A dermoscopic view of a skin lesion — 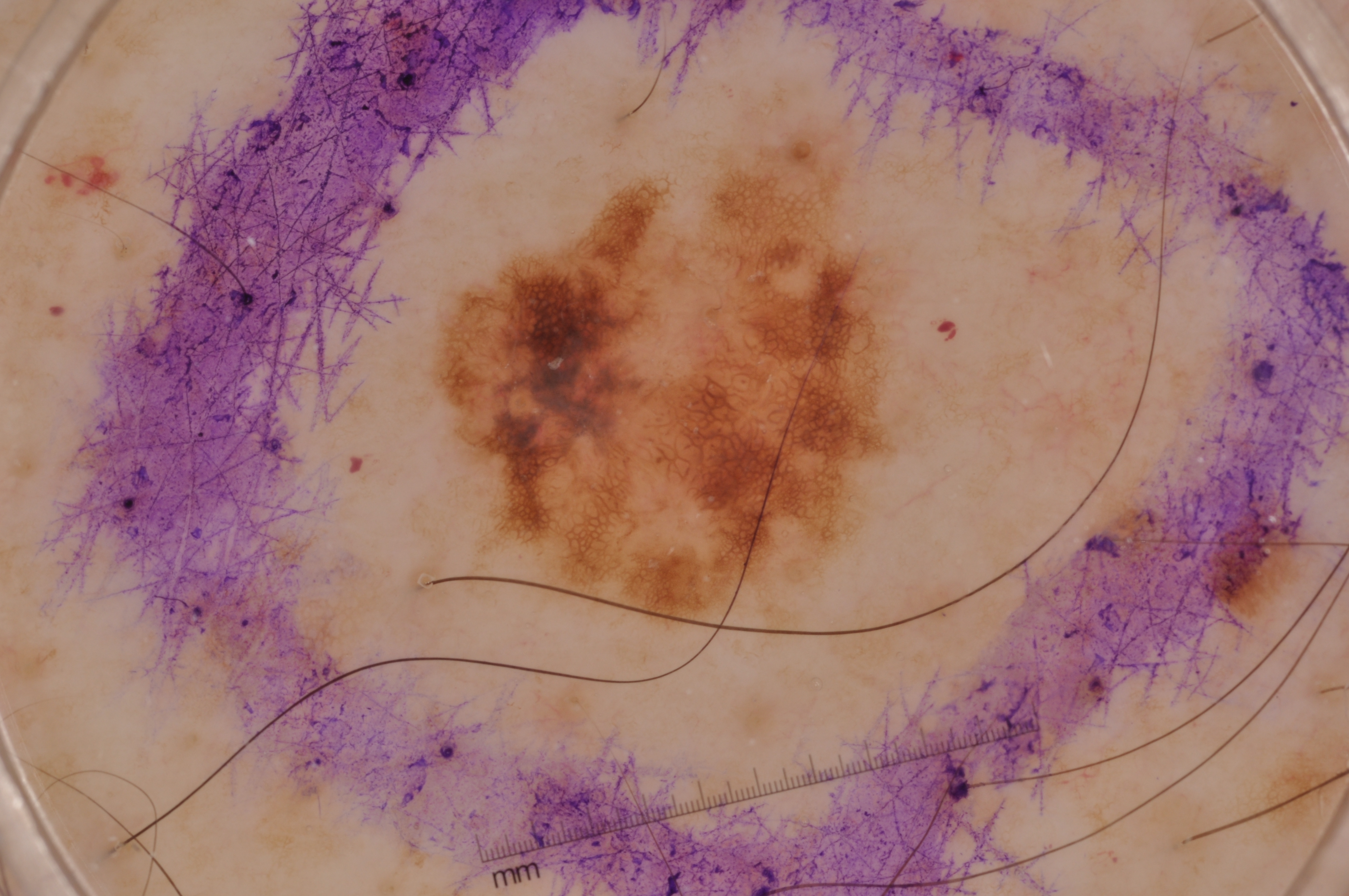Summary: The lesion occupies roughly 14% of the field. Dermoscopic review identifies pigment network, with no negative network, milia-like cysts, or streaks. With coordinates (x1, y1, x2, y2), the lesion occupies the region bbox=[422, 126, 896, 623]. Assessment: Consistent with a melanocytic nevus, a benign skin lesion.